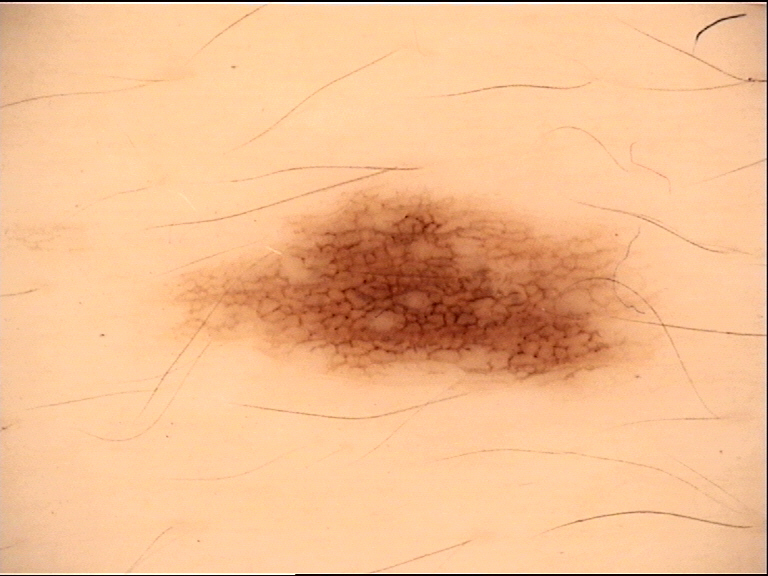label = junctional nevus (expert consensus)